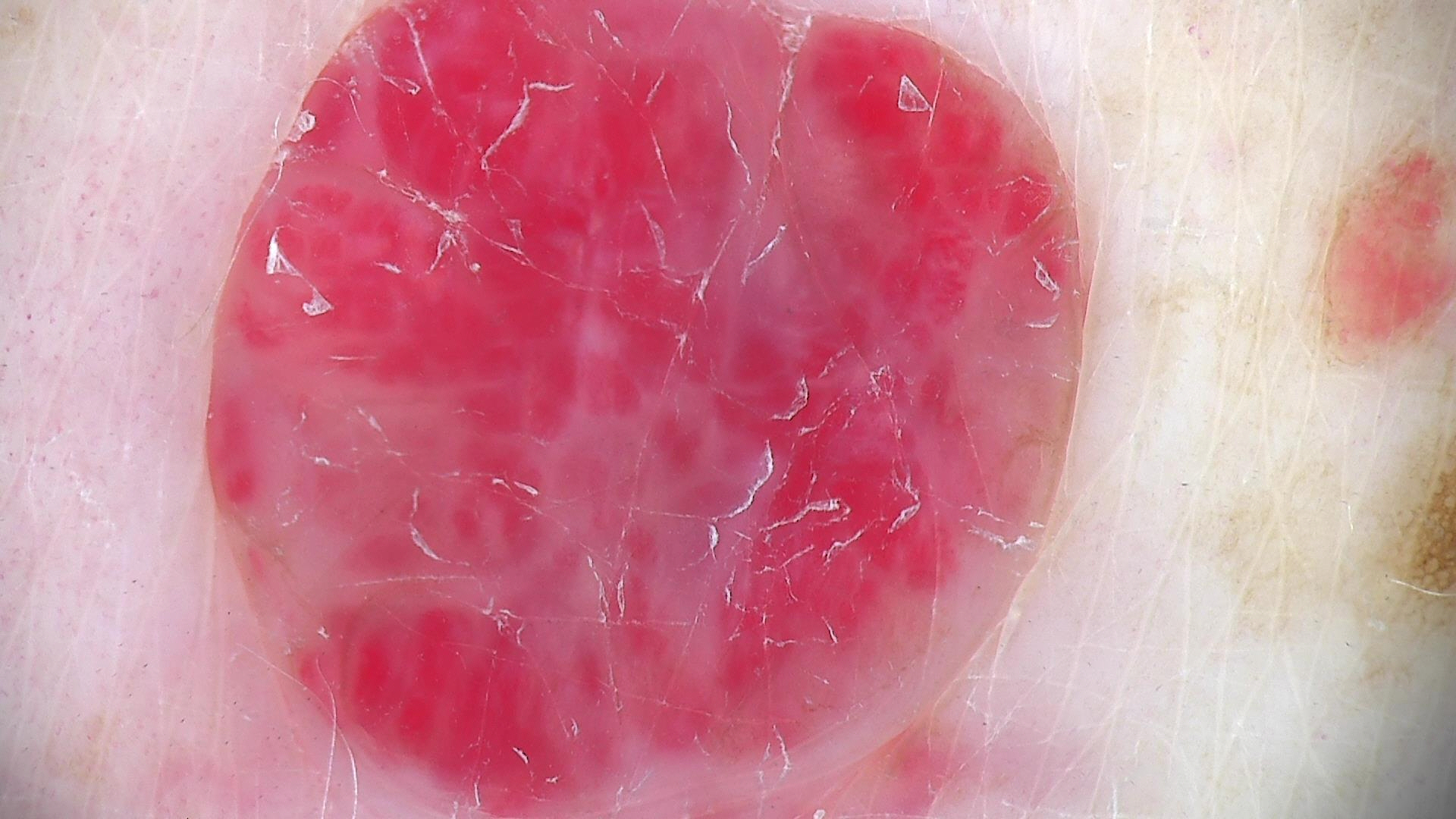Findings: A dermoscopic close-up of a skin lesion. This is a vascular lesion. Conclusion: The diagnostic label was a hemangioma.